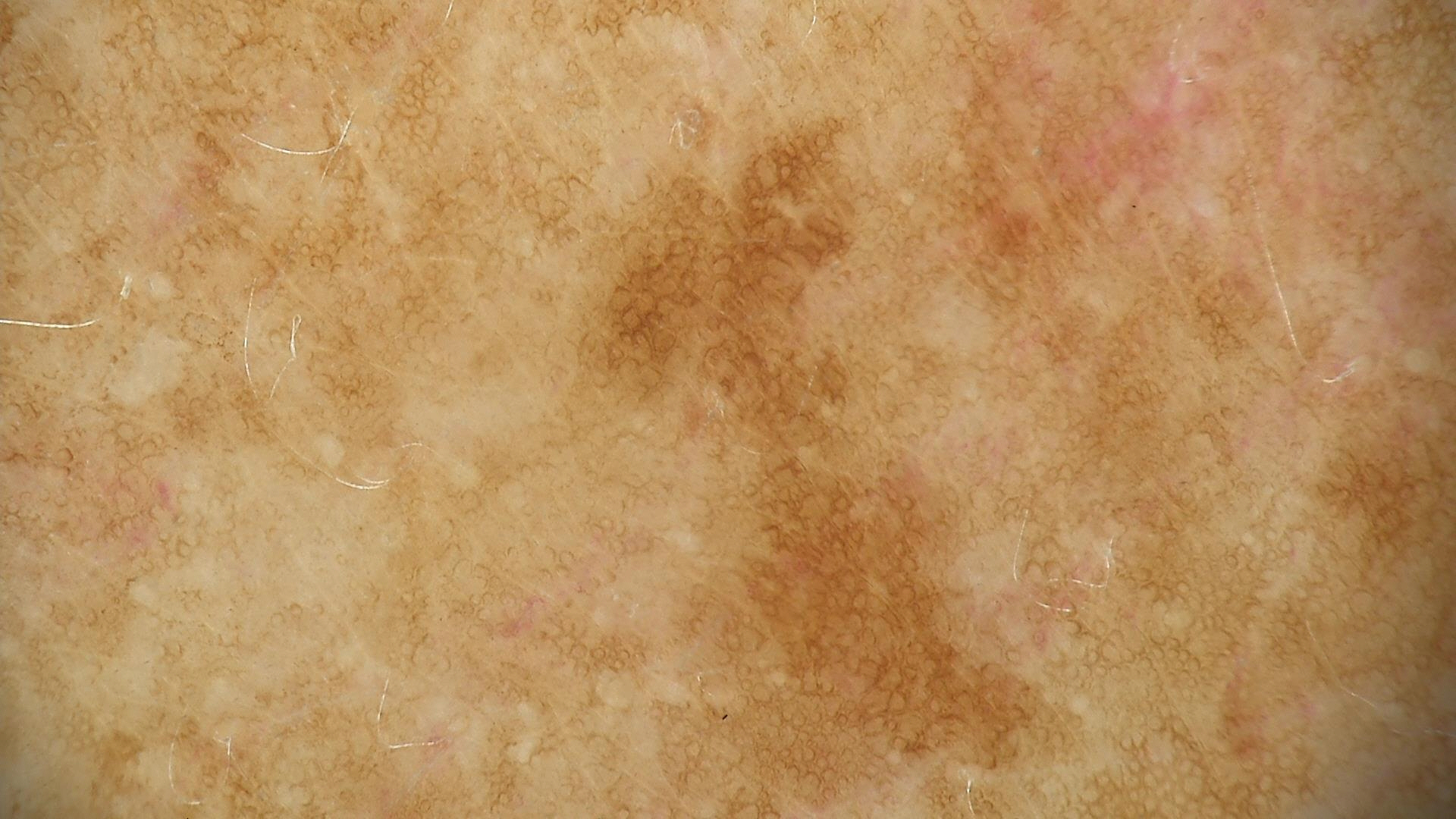Labeled as a solar lentigo.